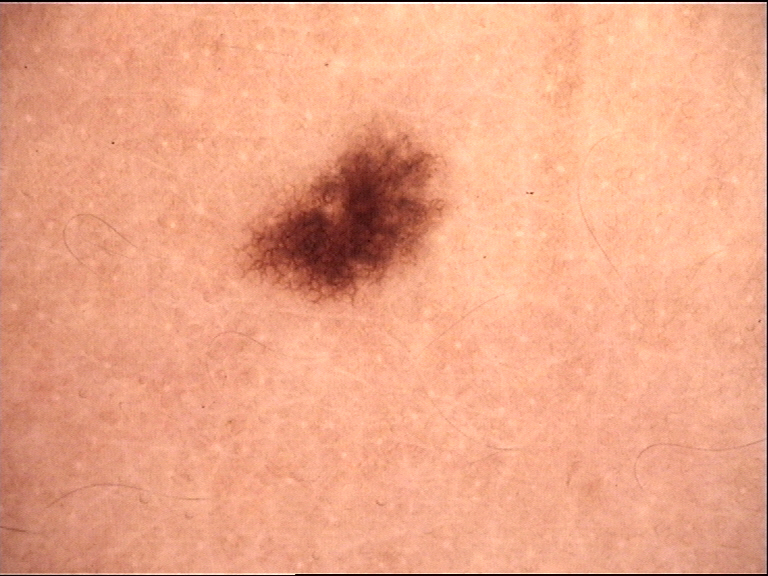Labeled as a dysplastic junctional nevus.